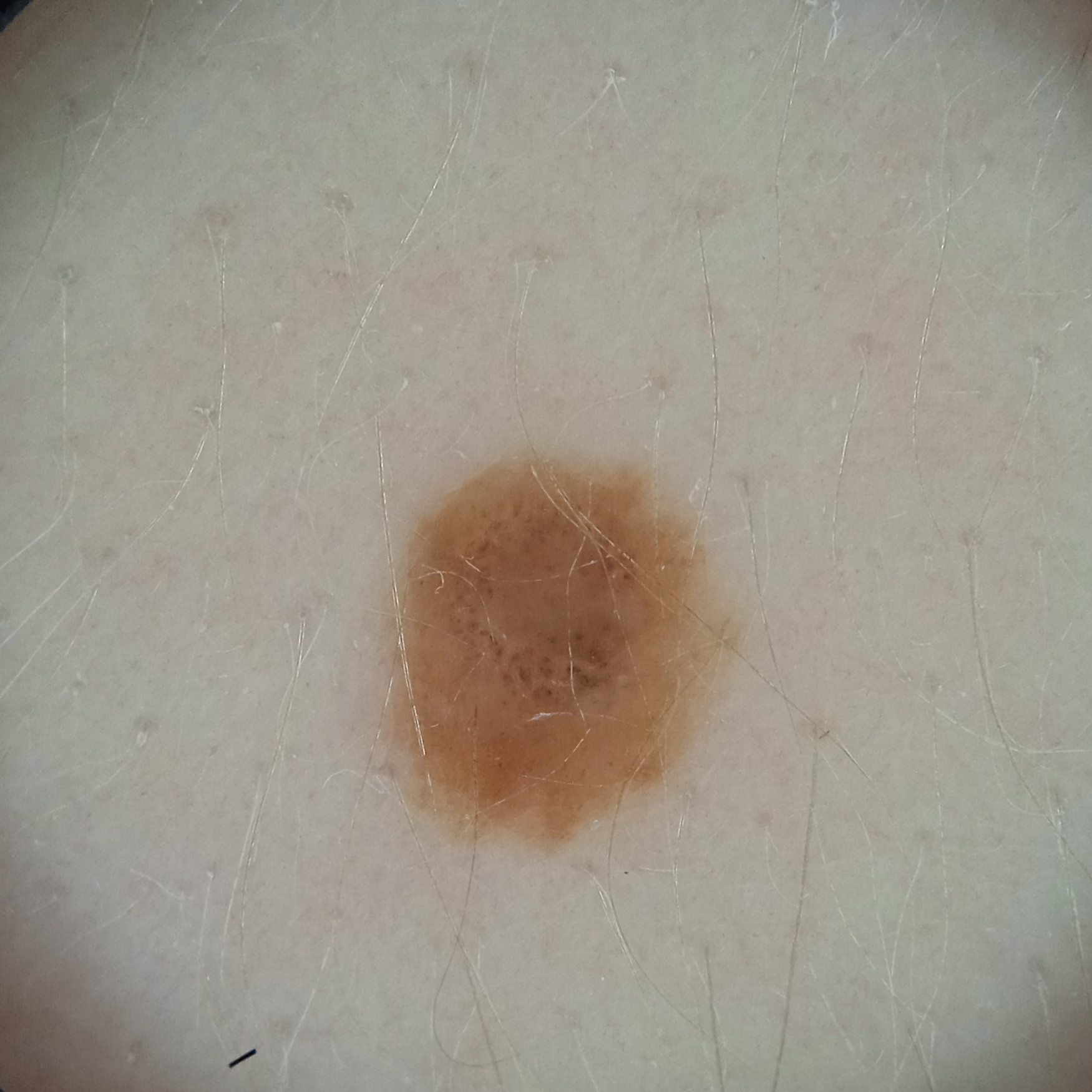{"image": "dermoscopy", "lesion_size": {"diameter_mm": 4.4}, "diagnosis": {"name": "melanocytic nevus", "malignancy": "benign"}}